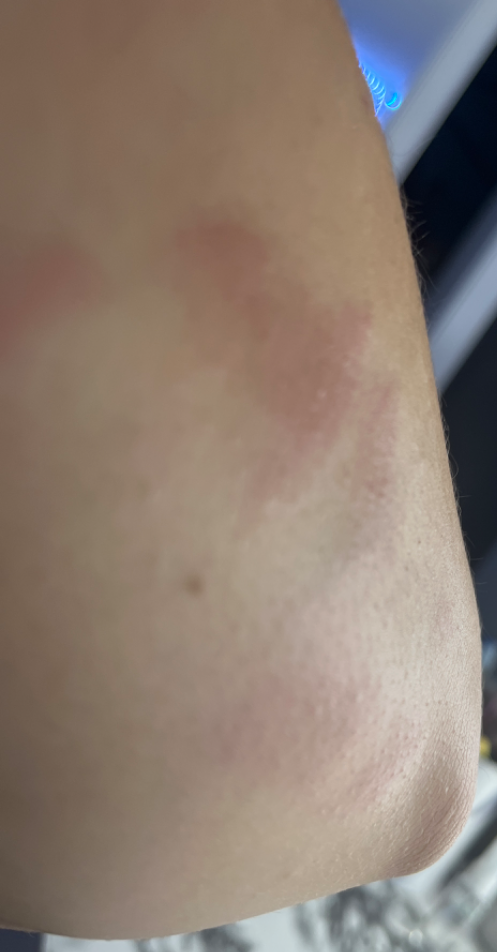assessment = ungradable on photographic review.